A dermoscopic image of a skin lesion.
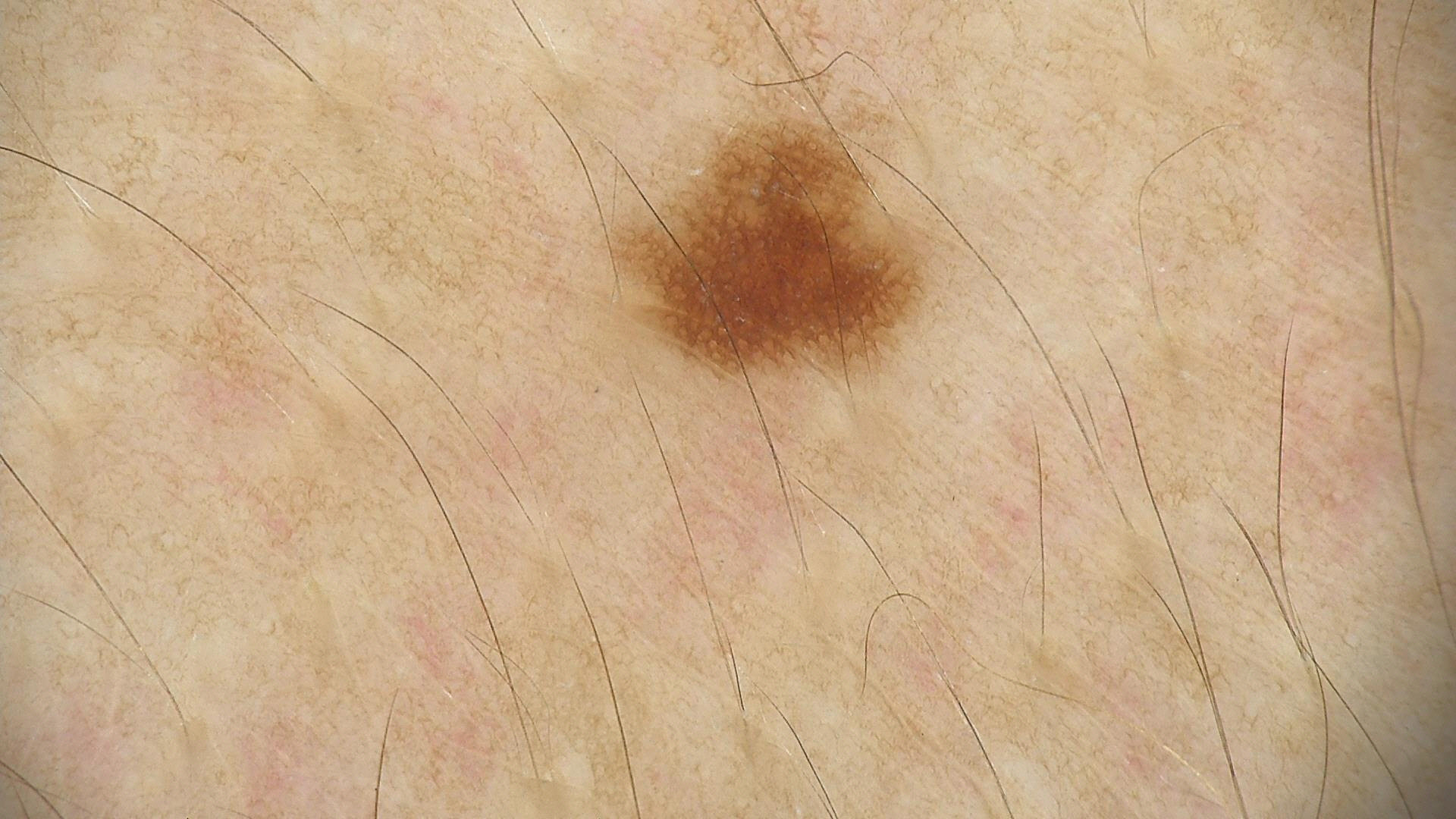Classified as a dysplastic junctional nevus.